The photograph is a close-up of the affected area; the affected area is the sole of the foot; the patient is a male aged 18–29.
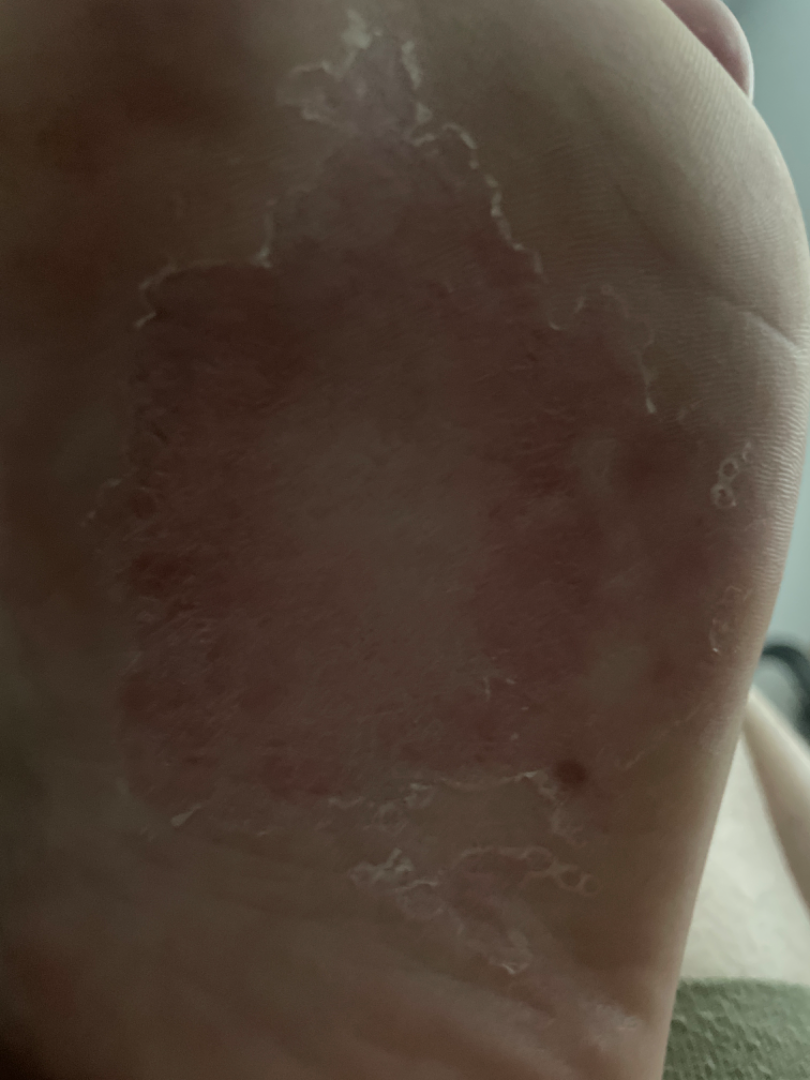{
  "assessment": "indeterminate"
}